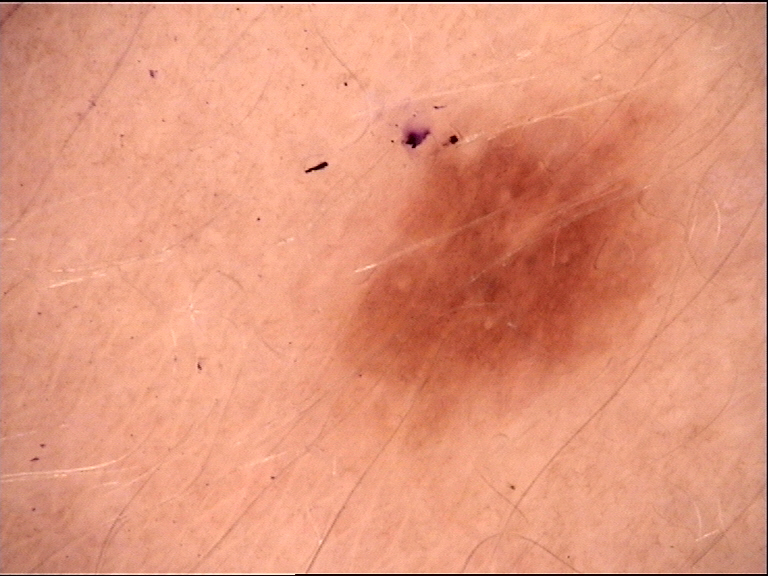A dermoscopy image of a single skin lesion. This is a banal lesion. Consistent with a junctional nevus.